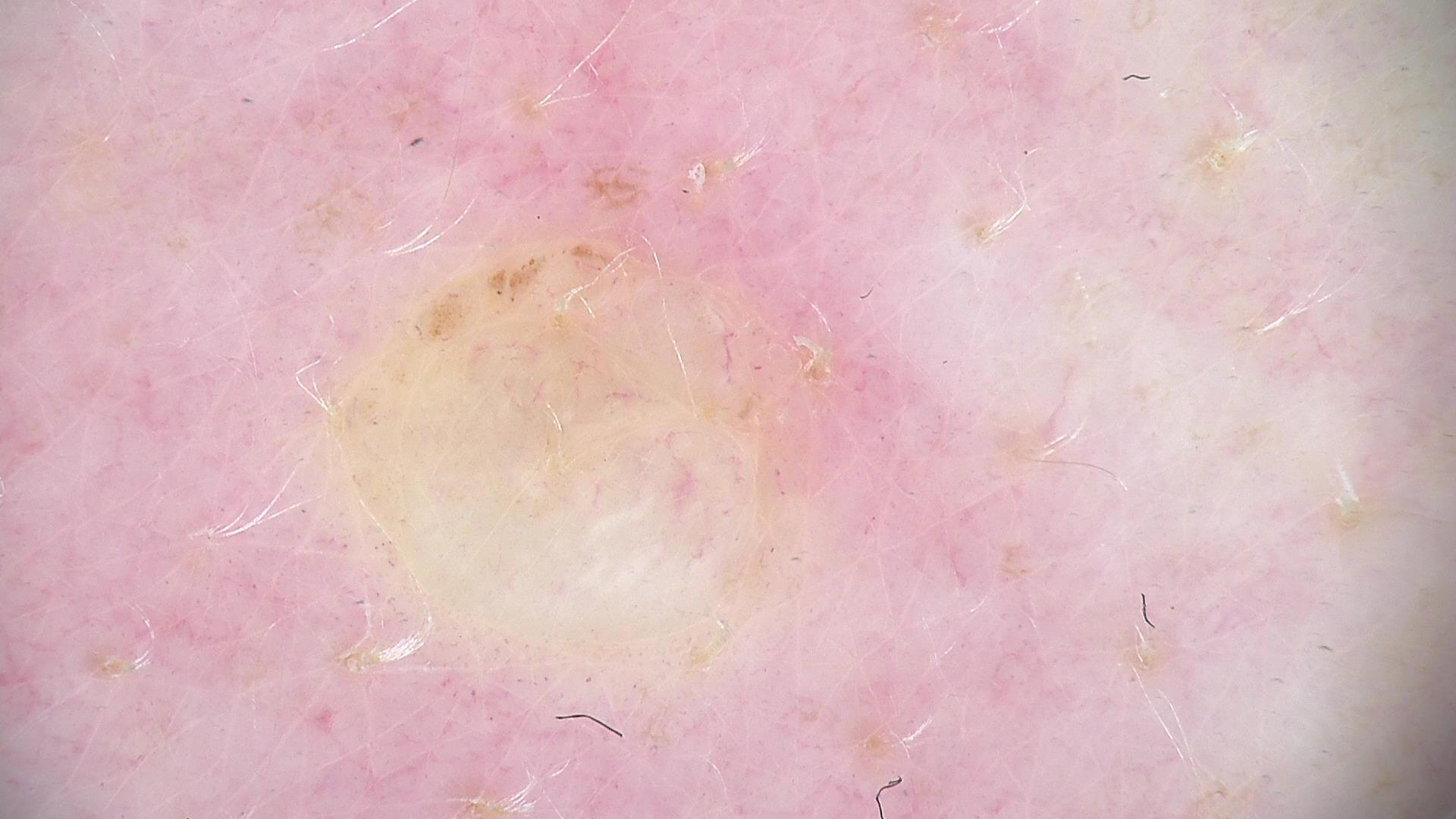A skin lesion imaged with a dermatoscope. Consistent with a banal lesion — a dermal nevus.